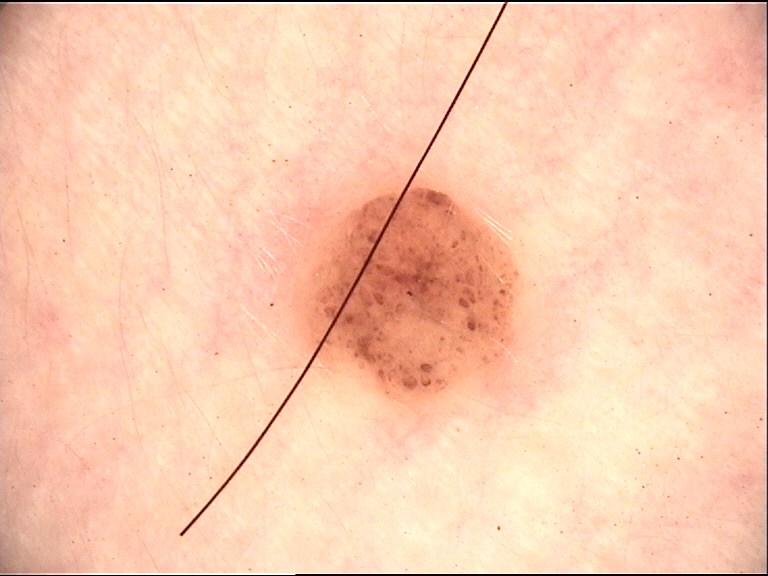The diagnosis was a dermal nevus.